A skin lesion imaged with a dermatoscope:
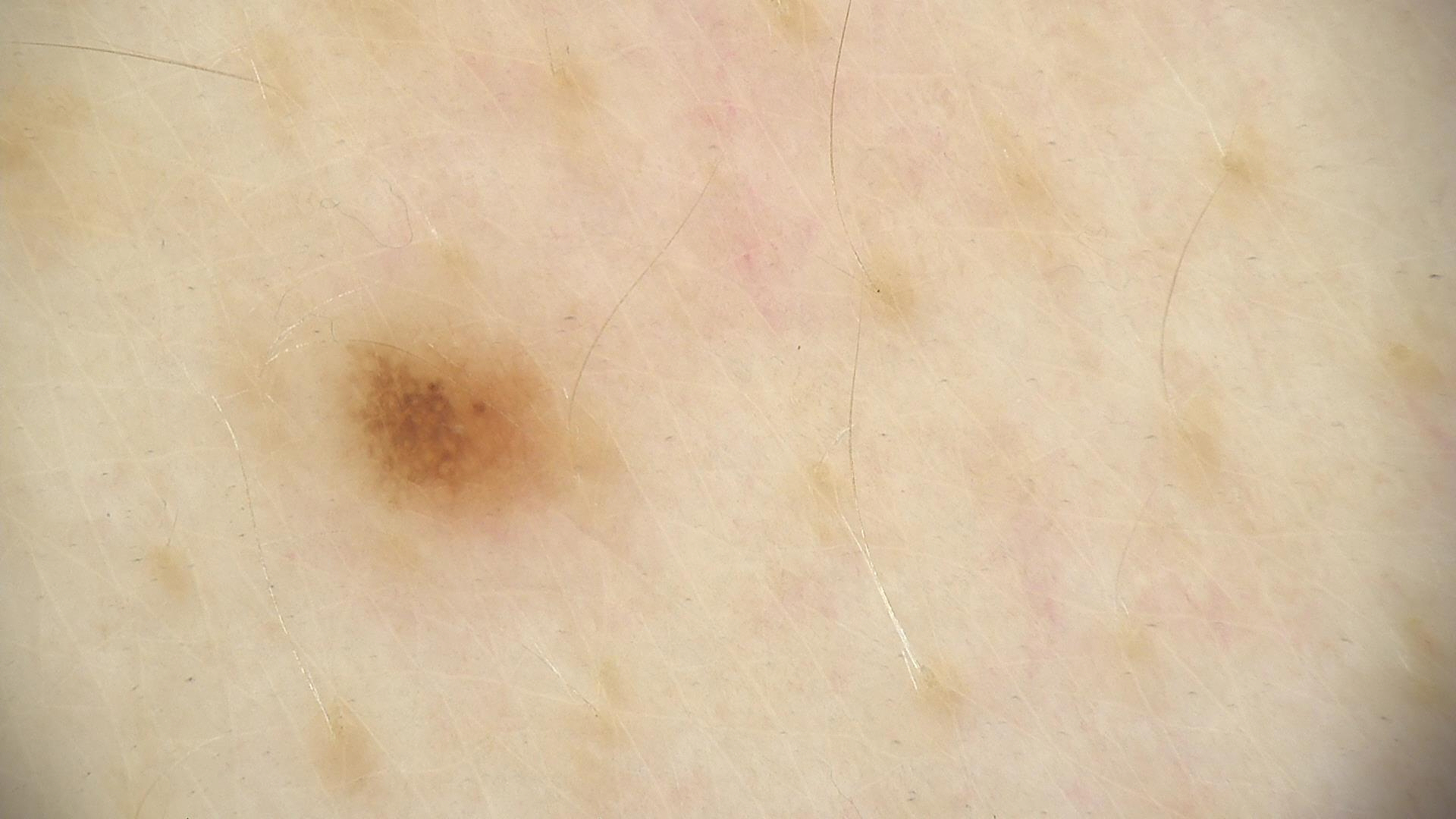Findings:
* class — dysplastic junctional nevus (expert consensus)